The lesion is described as rough or flaky. A close-up photograph. Female contributor, age 30–39 — 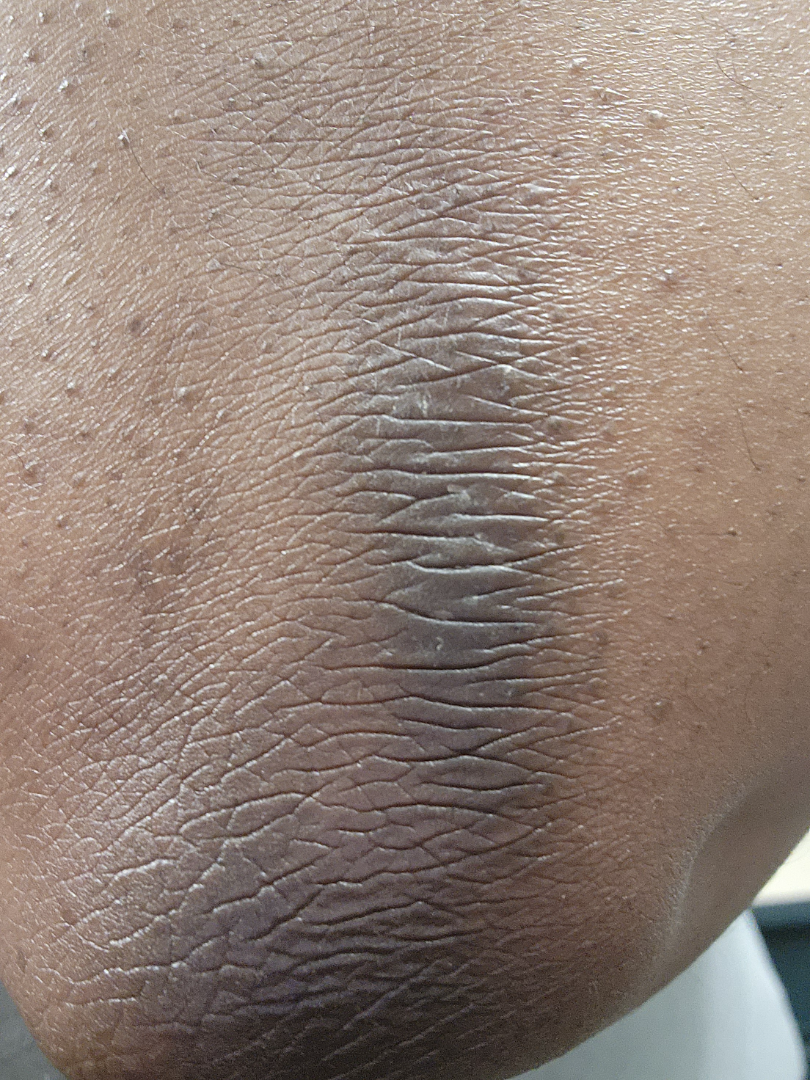assessment = Chronic dermatitis, NOS (primary).